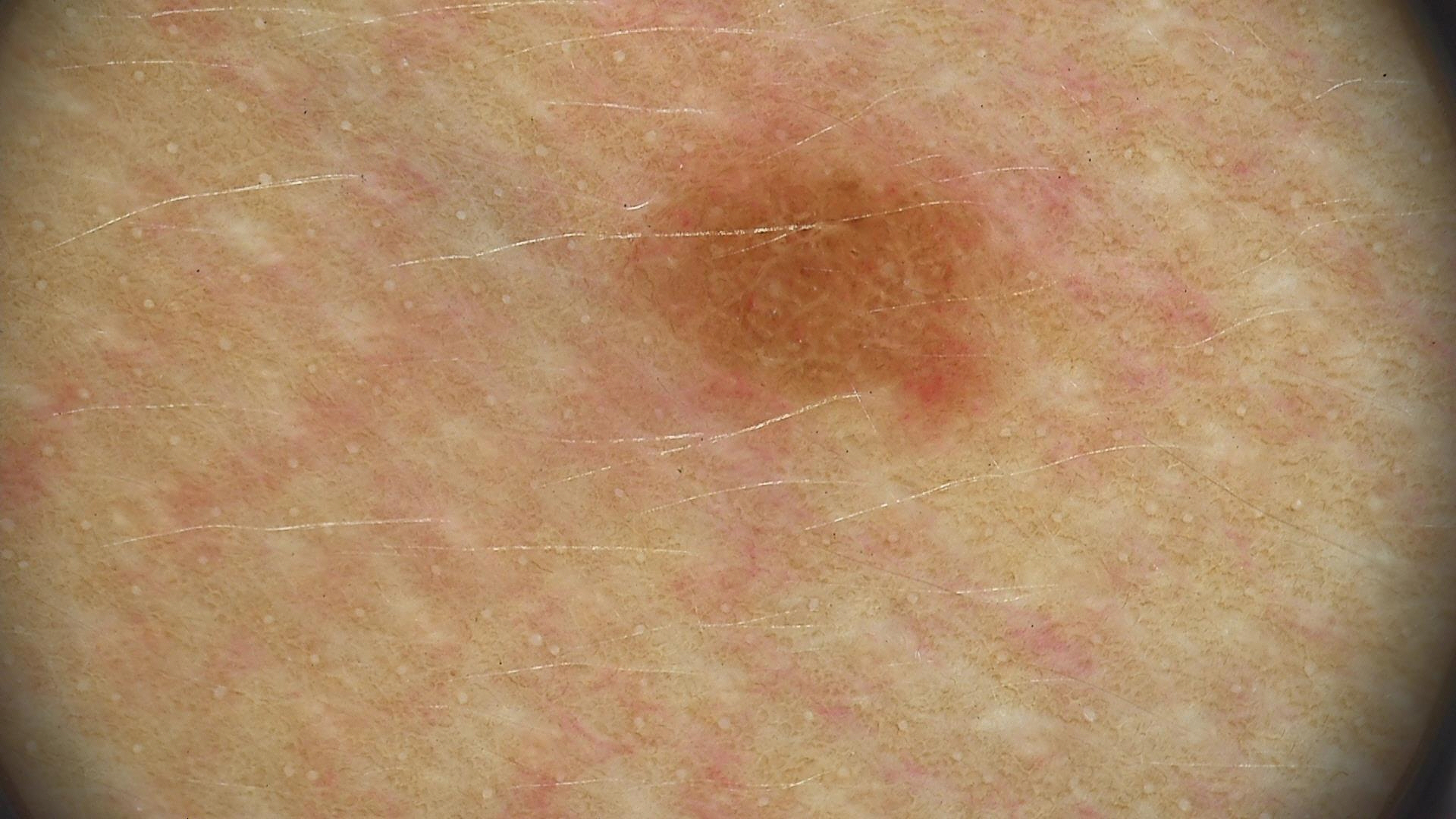Consistent with a banal lesion — a junctional nevus.